Symptoms reported: pain, burning and itching · located on the back of the torso · the condition has been present for less than one week · a close-up photograph.
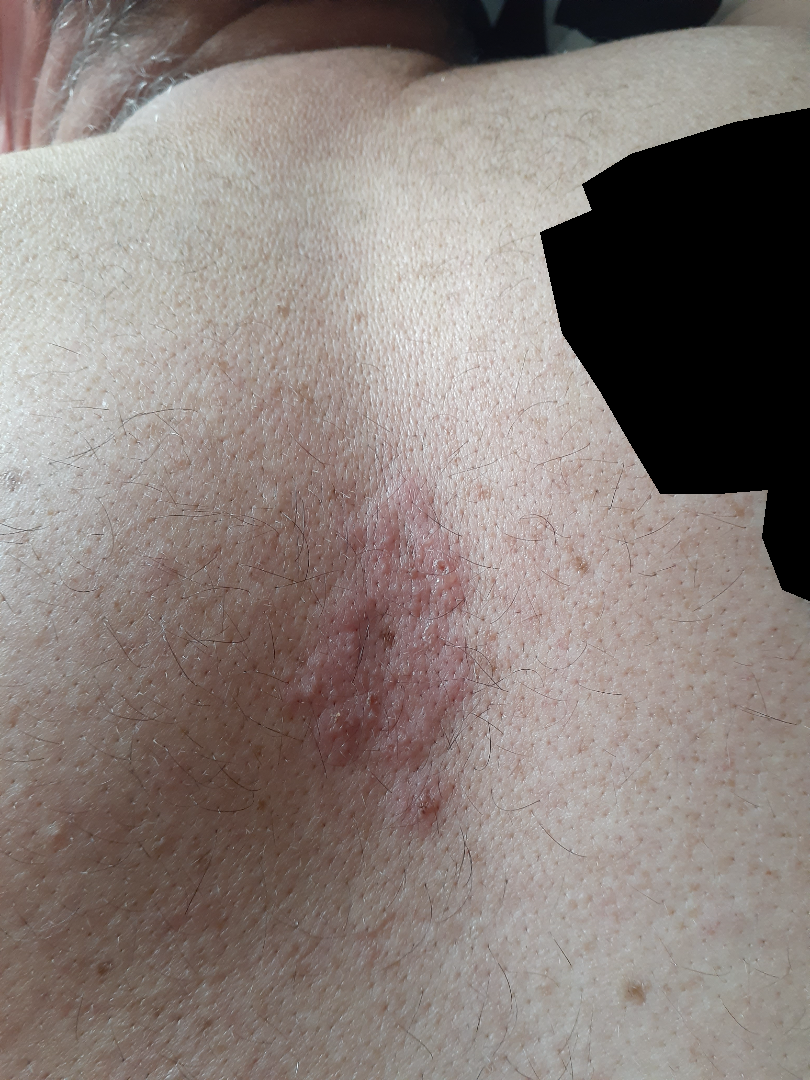{
  "assessment": "ungradable on photographic review"
}